A dermoscopic image of a skin lesion:
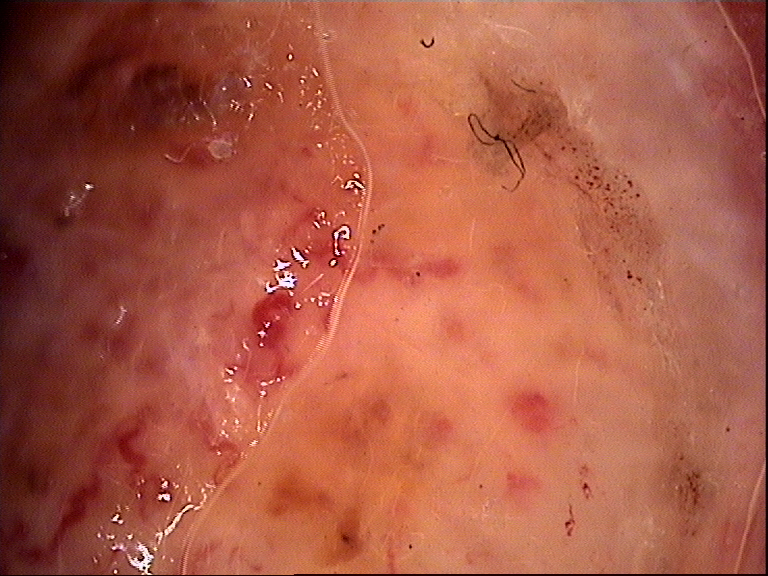Findings: The architecture is that of a keratinocytic lesion. Pathology: Biopsy-confirmed as a skin cancer — a basal cell carcinoma.